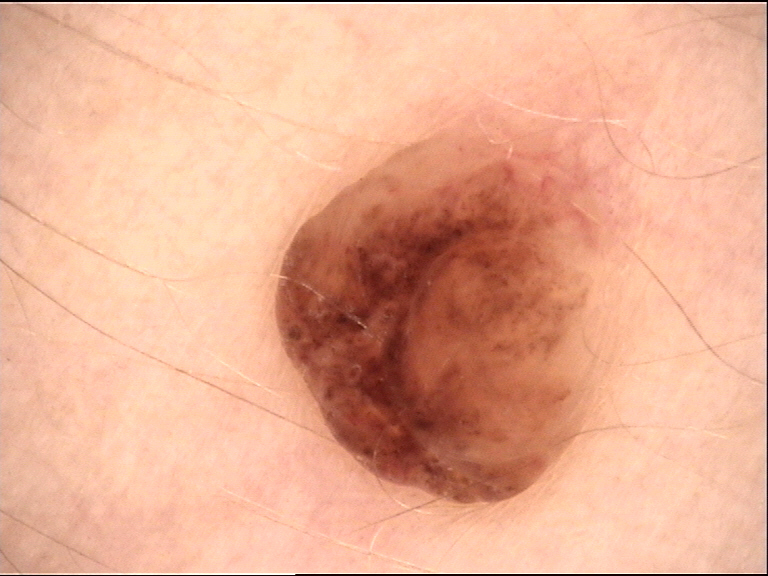Dermoscopy of a skin lesion. Diagnosed as a banal lesion — a dermal nevus.